Dermoscopy of a skin lesion.
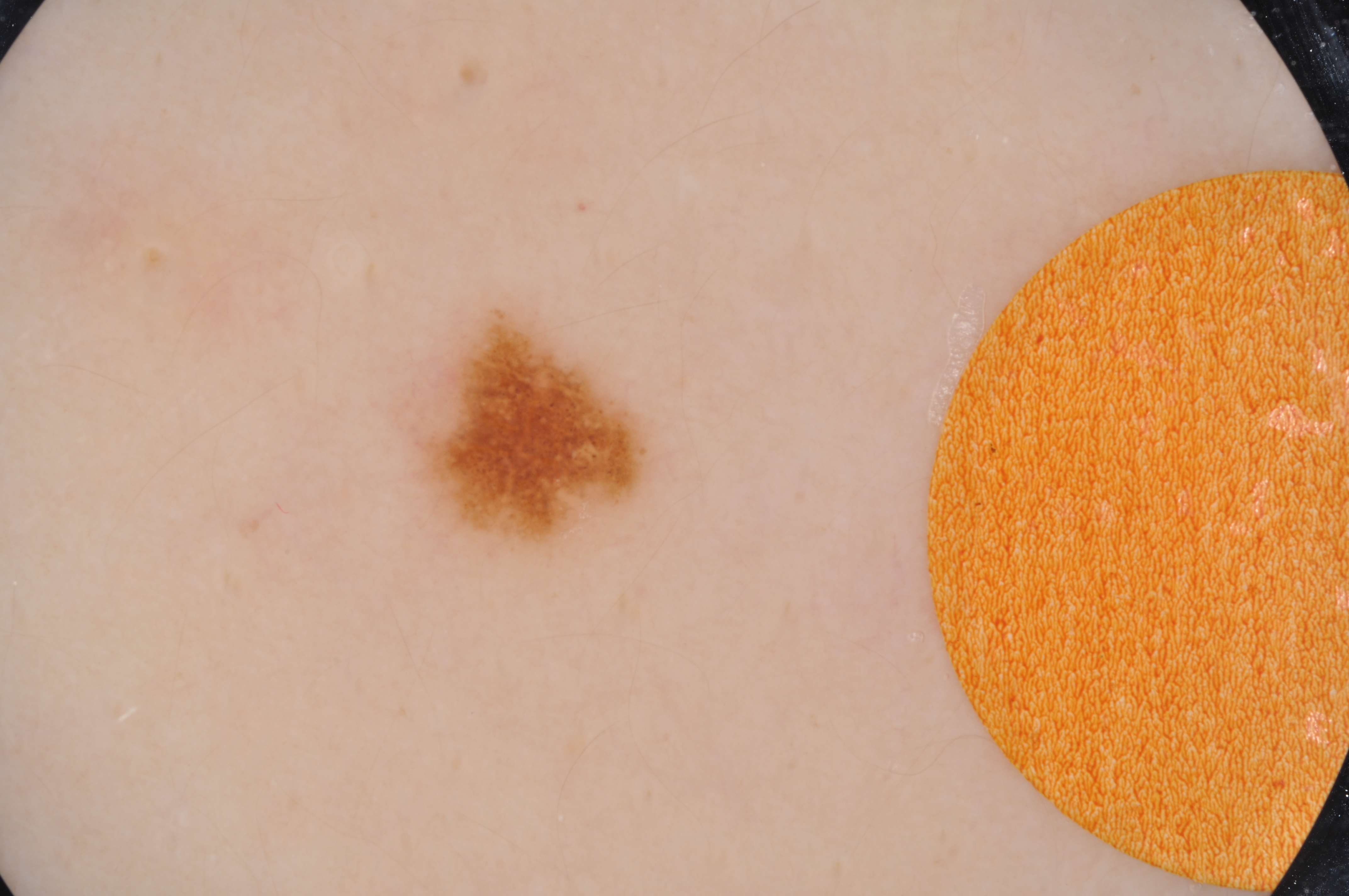With coordinates (x1, y1, x2, y2), the lesion spans 415 308 651 550. The lesion takes up about 3% of the image. Dermoscopic review identifies pigment network; no globules, negative network, streaks, or milia-like cysts. Diagnosed as a melanocytic nevus.